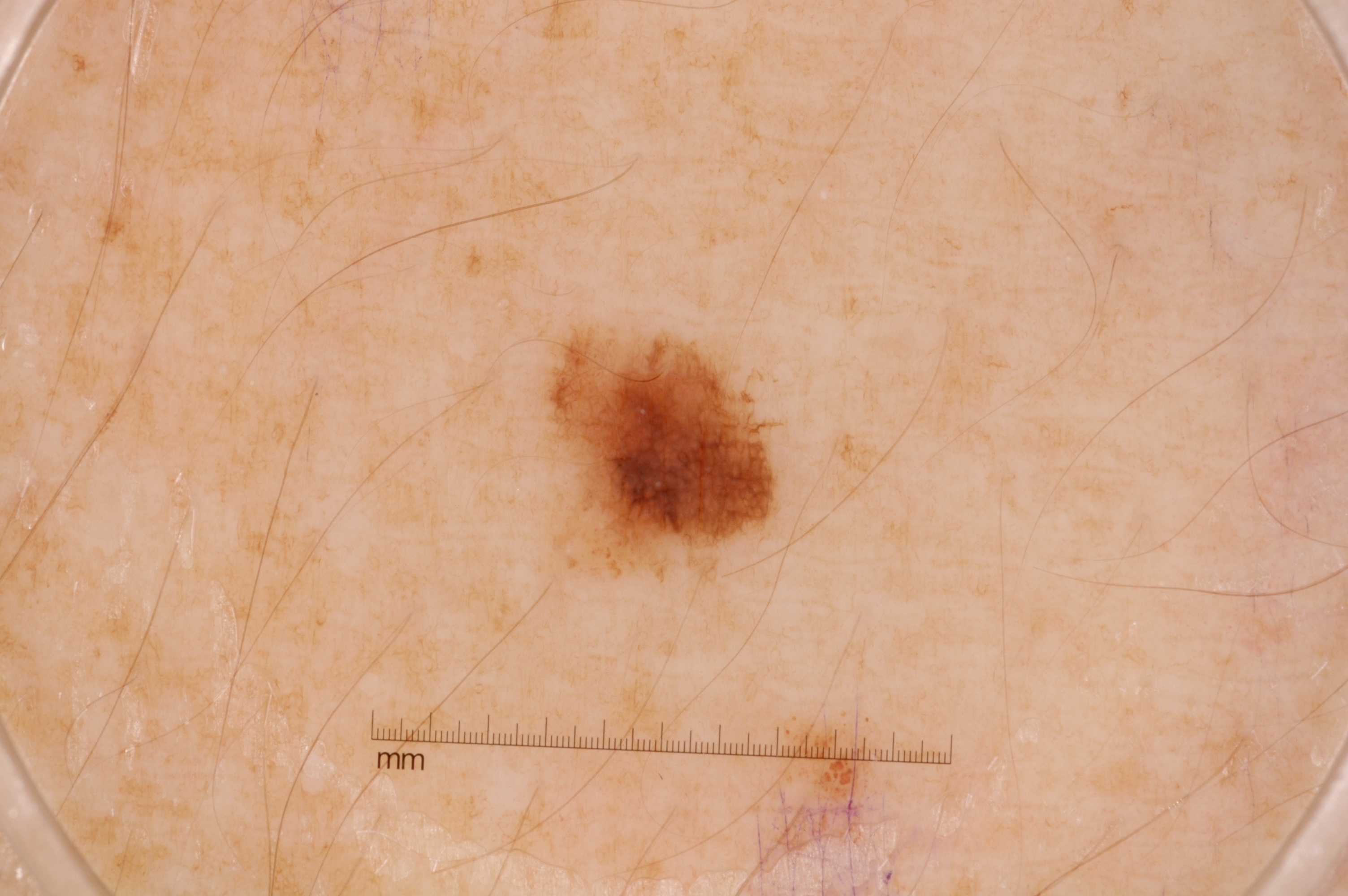<case>
<image>
  <modality>dermoscopy</modality>
</image>
<patient>
  <sex>female</sex>
  <age_approx>50</age_approx>
</patient>
<dermoscopic_features>
  <present>pigment network</present>
  <absent>streaks, negative network, milia-like cysts</absent>
</dermoscopic_features>
<lesion_location>
  <bbox_xyxy>516, 321, 786, 587</bbox_xyxy>
</lesion_location>
<lesion_extent>
  <approx_field_fraction_pct>4</approx_field_fraction_pct>
</lesion_extent>
<diagnosis>
  <name>melanocytic nevus</name>
  <malignancy>benign</malignancy>
  <lineage>melanocytic</lineage>
  <provenance>clinical</provenance>
</diagnosis>
</case>